A clinical close-up photograph of a skin lesion. A subject 22 years old.
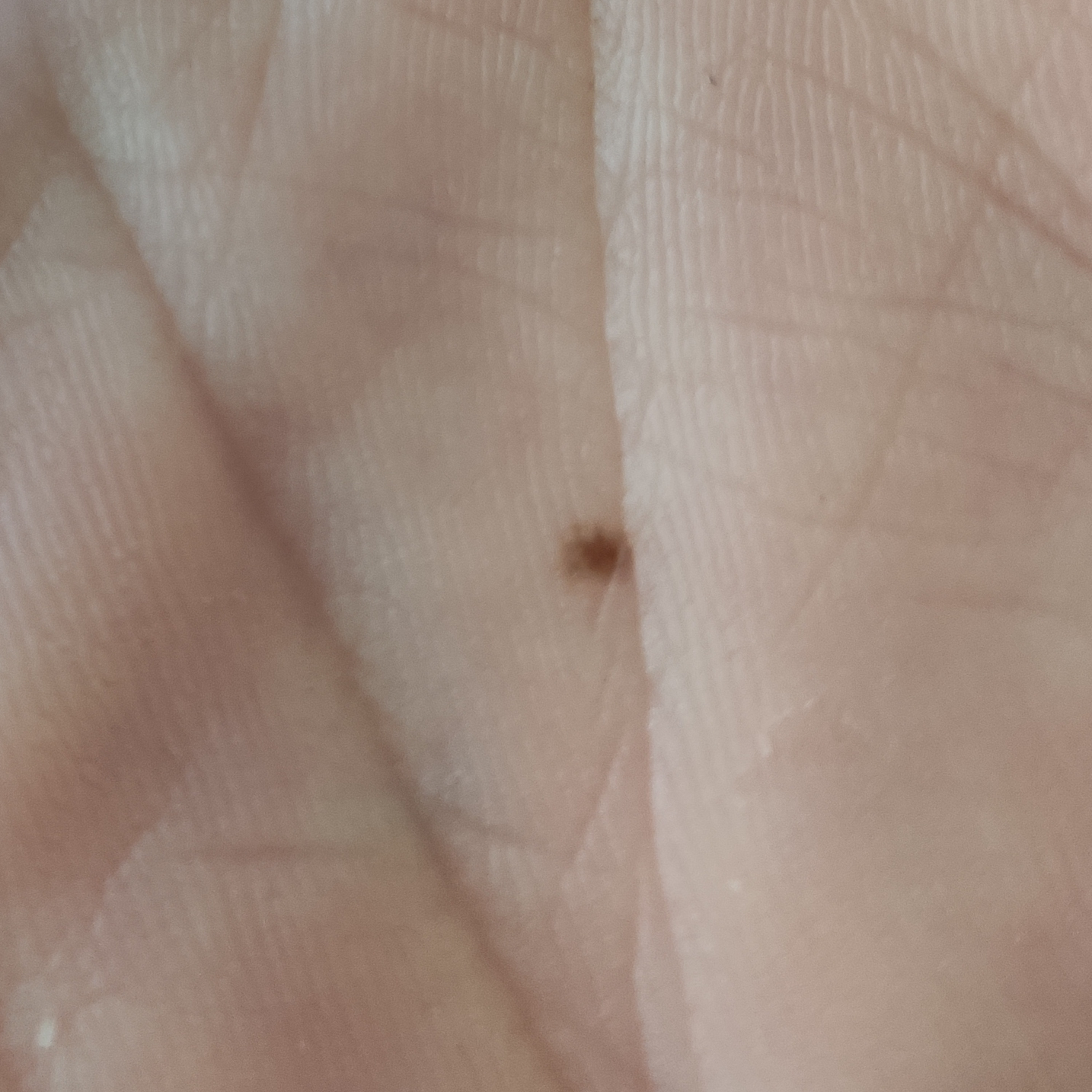region: a hand
reported symptoms: change in appearance, growth / no elevation, no pain
diagnosis: nevus (clinical consensus)